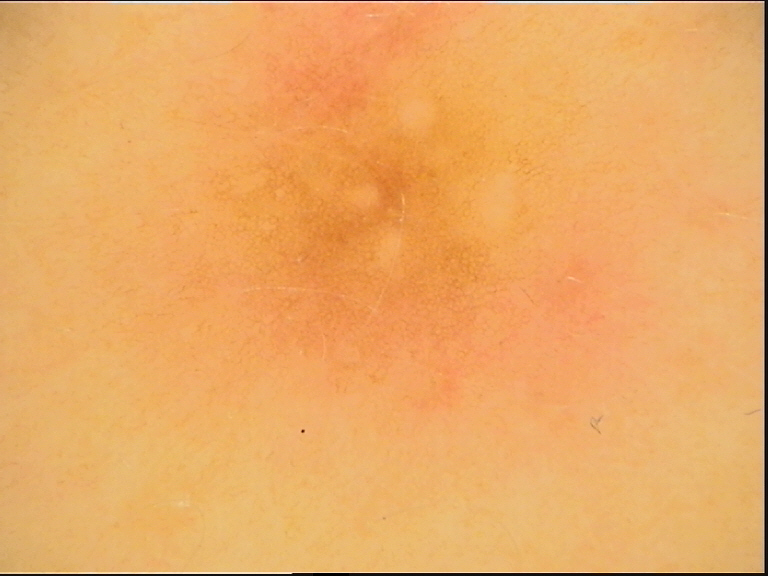A dermoscopic image of a skin lesion.
The architecture is that of a banal lesion.
Consistent with a junctional nevus.